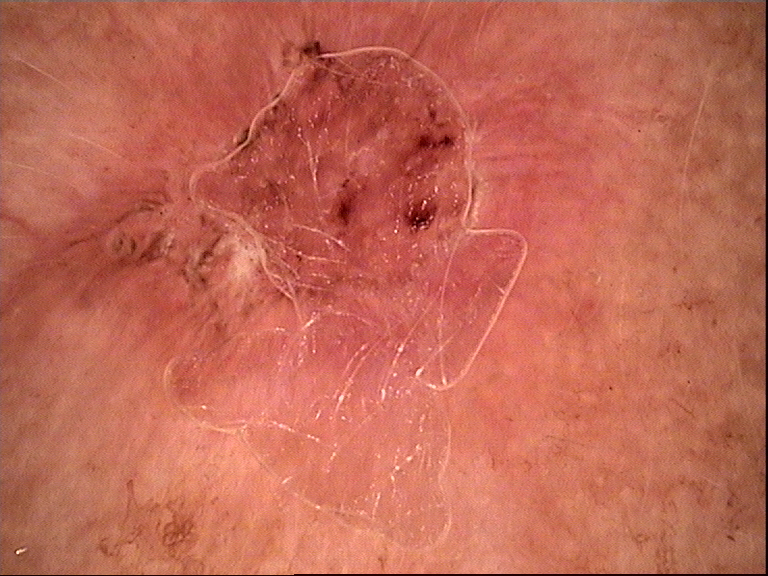| field | value |
|---|---|
| class | basal cell carcinoma (biopsy-proven) |